A dermoscopic image of a skin lesion.
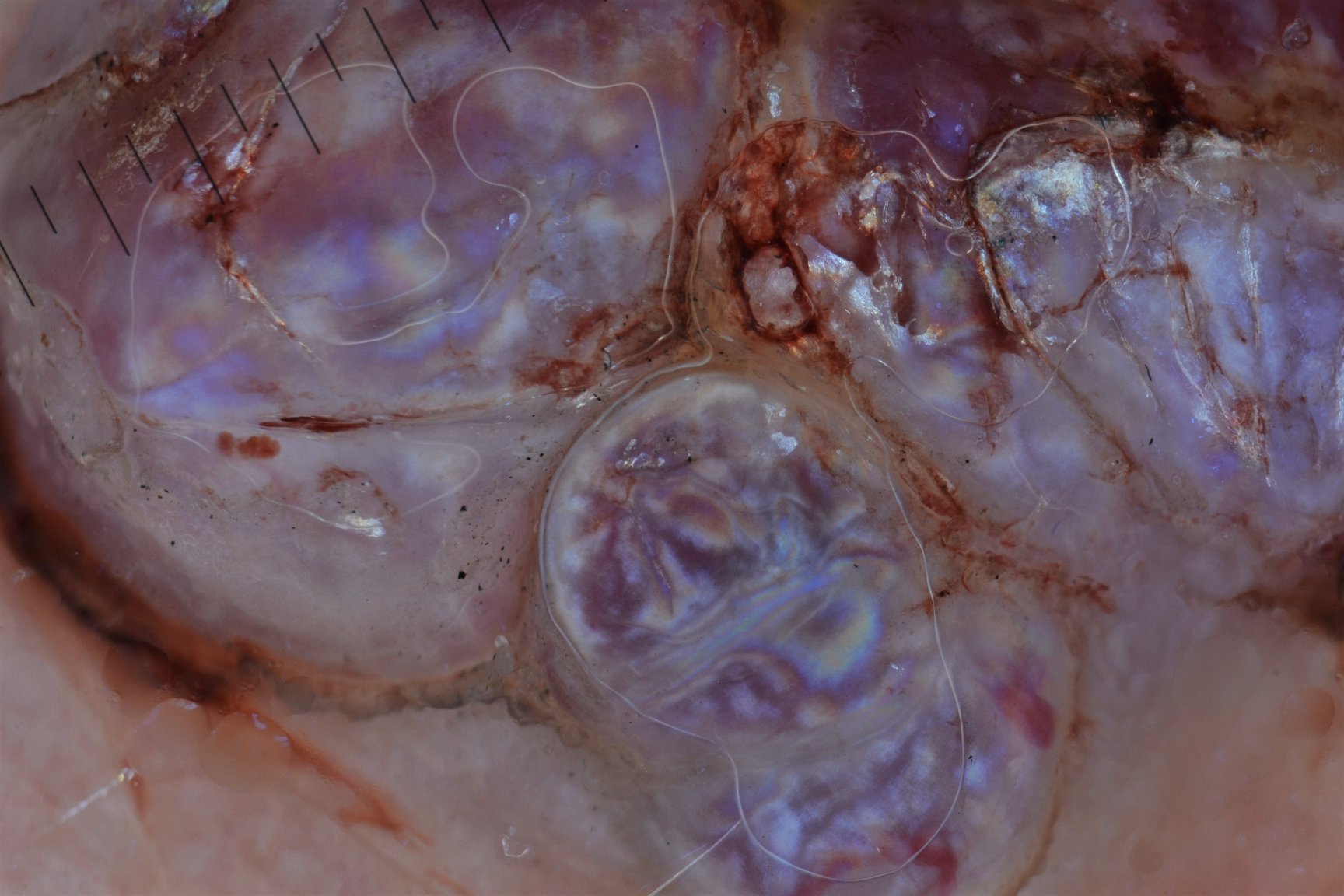| feature | finding |
|---|---|
| classification | vascular |
| diagnosis | Kaposi sarcoma (biopsy-proven) |